The photograph was taken at an angle · the contributor is female:
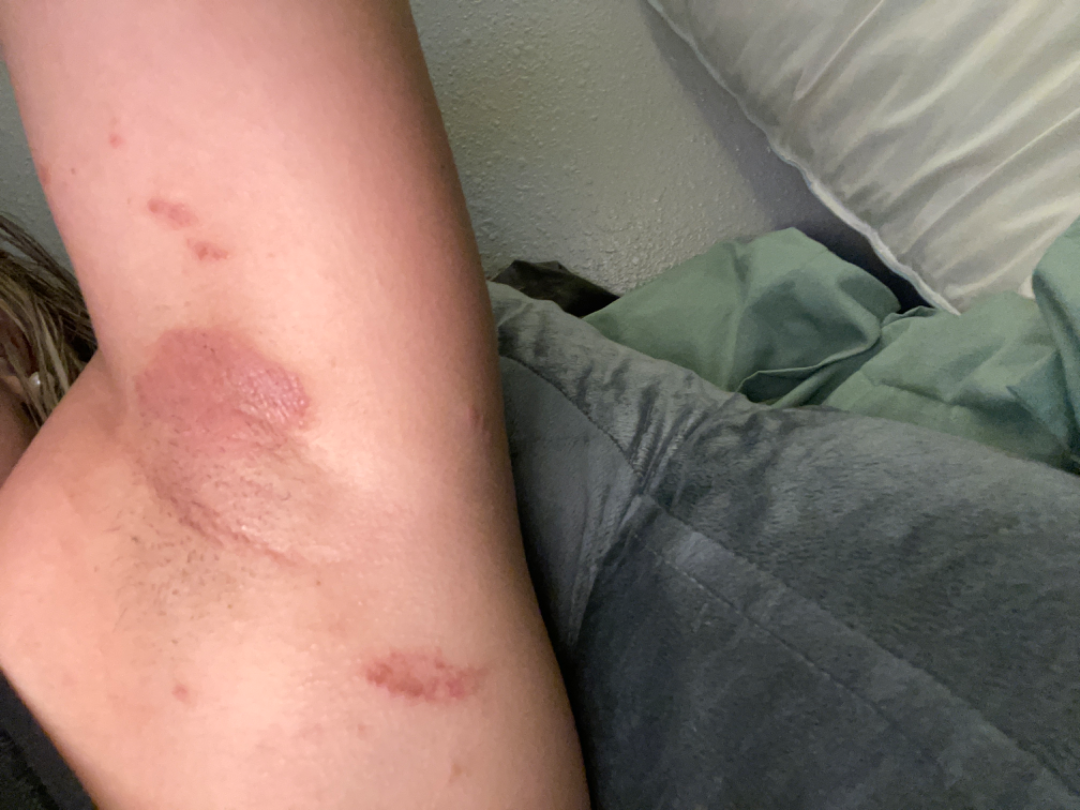The lesion is described as rough or flaky.
The patient described the issue as a rash.
Skin tone: FST III.
Symptoms reported: bothersome appearance and itching.
Present for three to twelve months.
On dermatologist assessment of the image: Allergic Contact Dermatitis and Irritant Contact Dermatitis were considered with similar weight.